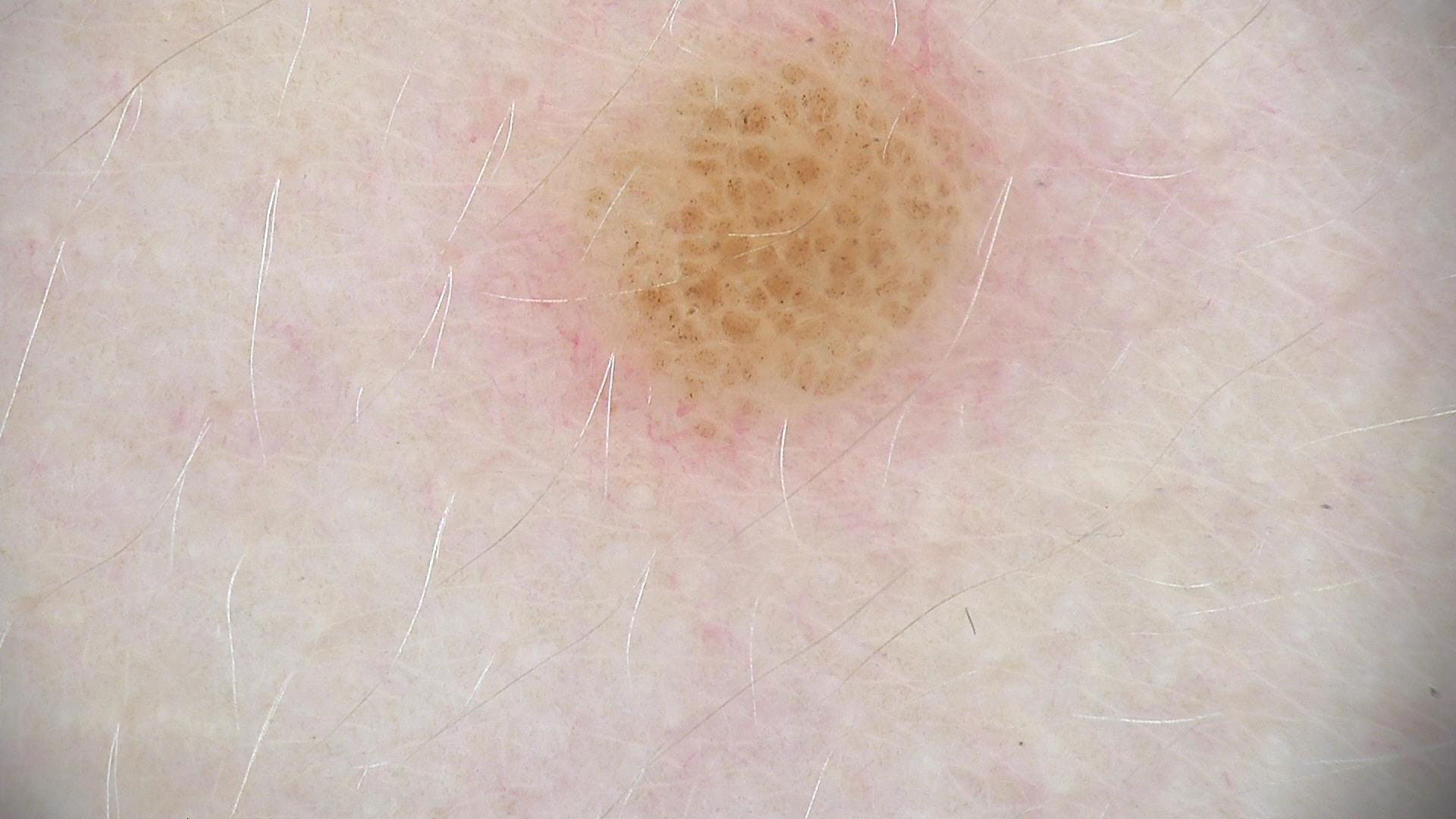imaging: dermatoscopy
category: banal
class: compound nevus (expert consensus)